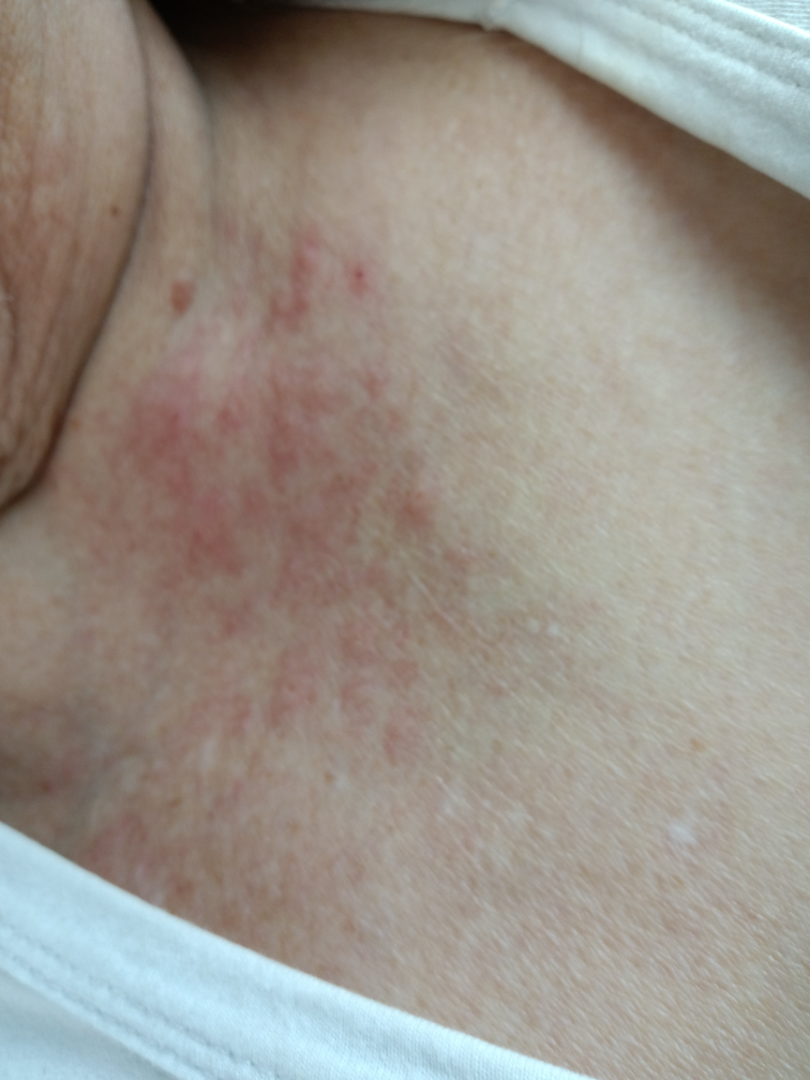The reviewing clinician's impression was: most consistent with Irritant Contact Dermatitis.